The affected area is the head or neck and arm. The photograph is a close-up of the affected area — 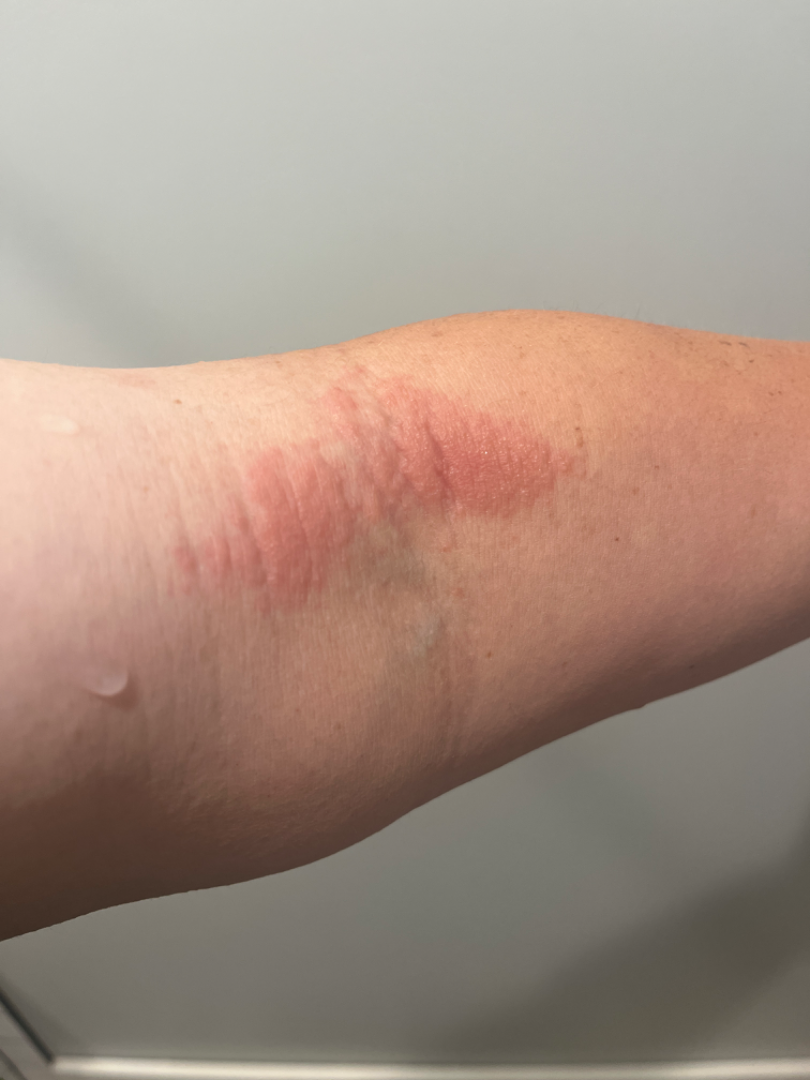- other reported symptoms: none reported
- reported symptoms: itching
- surface texture: raised or bumpy
- skin tone: Fitzpatrick skin type II; lay graders estimated MST 3 (US pool) or 2 (India pool)
- patient's own categorization: a rash
- symptom duration: less than one week
- dermatologist impression: in keeping with Eczema